The subject is a female aged 40–49, the affected area is the arm, close-up view.
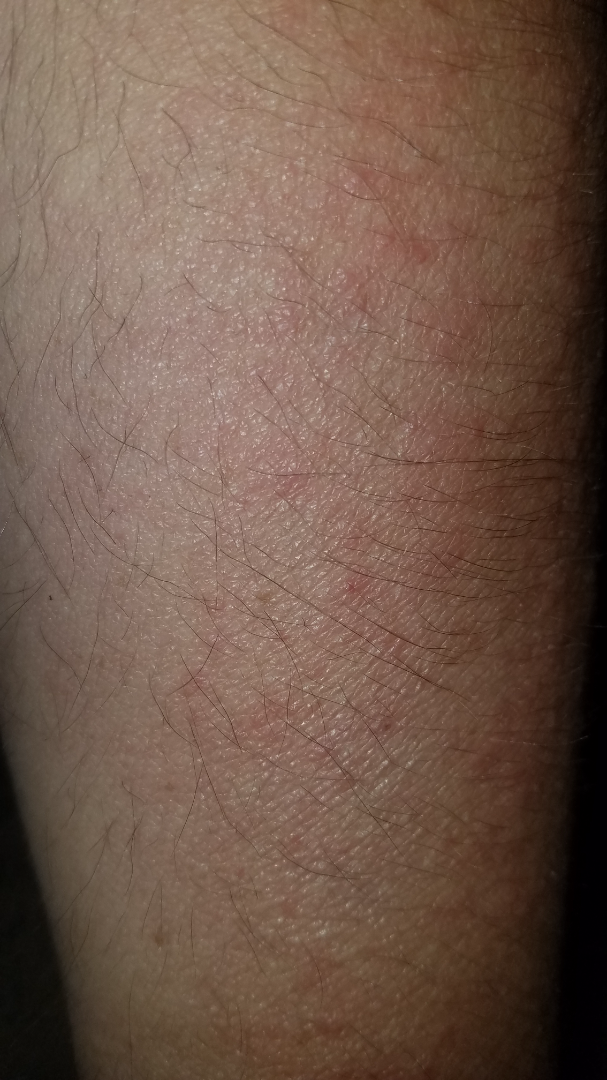Q: Could the case be diagnosed?
A: unable to determine